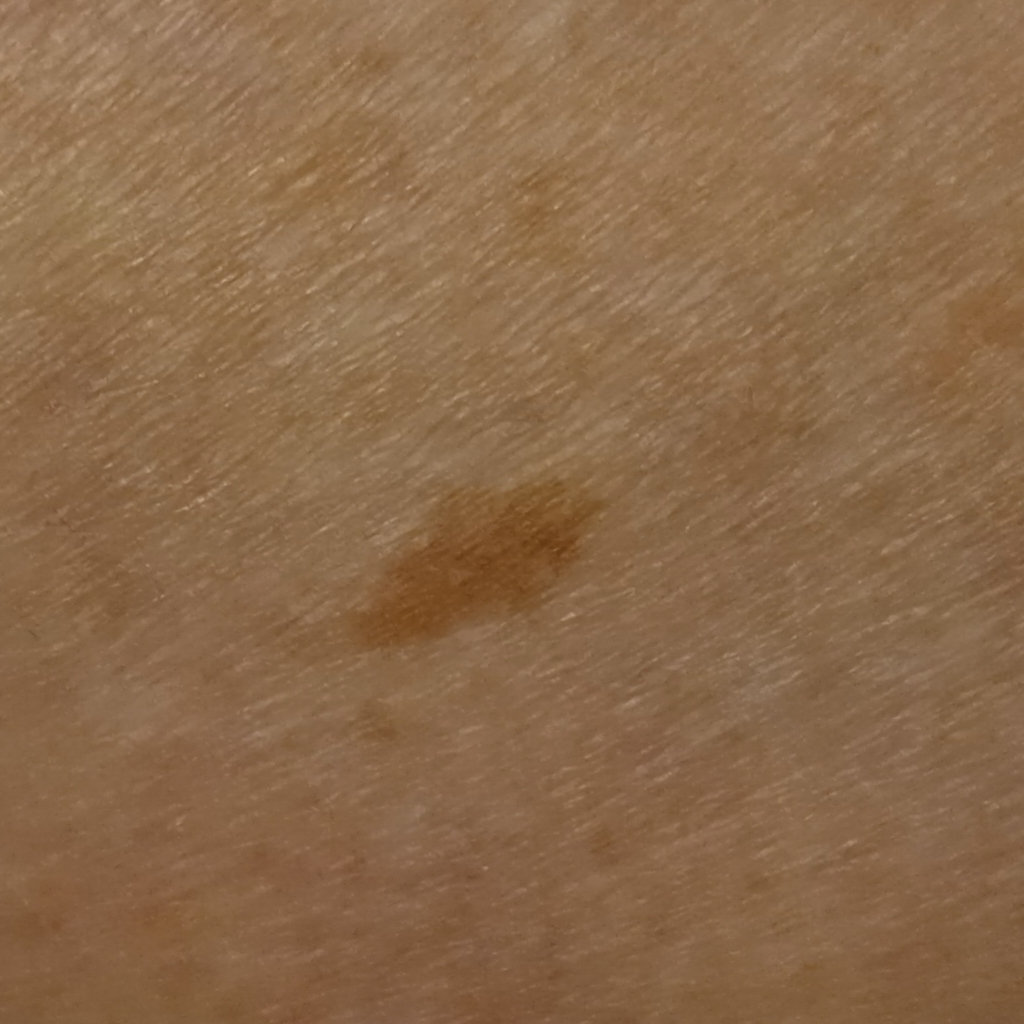<record>
<patient>
<age>75</age>
<sex>female</sex>
</patient>
<lesion_location>a leg</lesion_location>
<lesion_size>
<diameter_mm>8.2</diameter_mm>
</lesion_size>
<diagnosis>
<name>melanocytic nevus</name>
<malignancy>benign</malignancy>
</diagnosis>
</record>